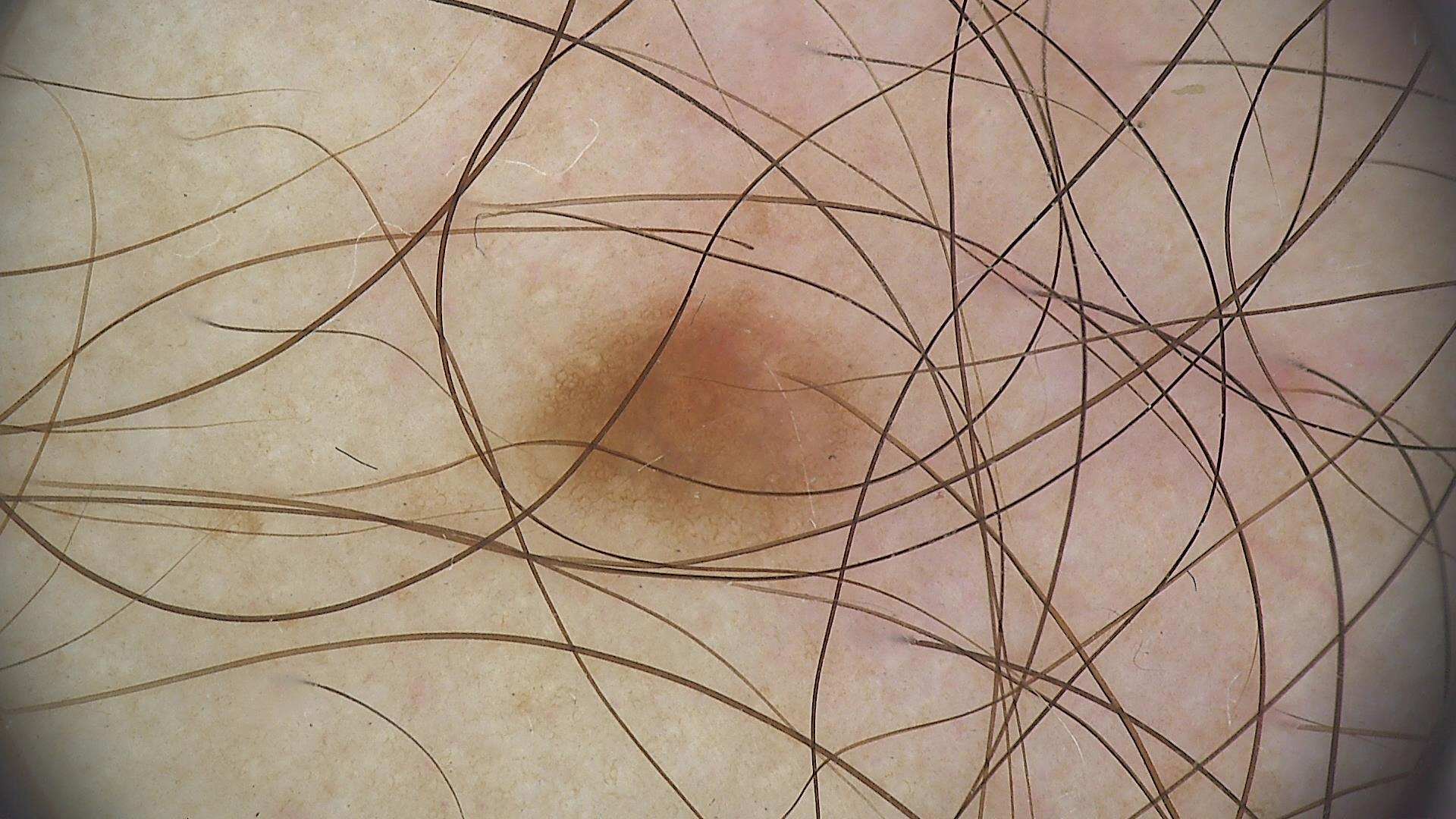Conclusion: The diagnostic label was a dysplastic junctional nevus.